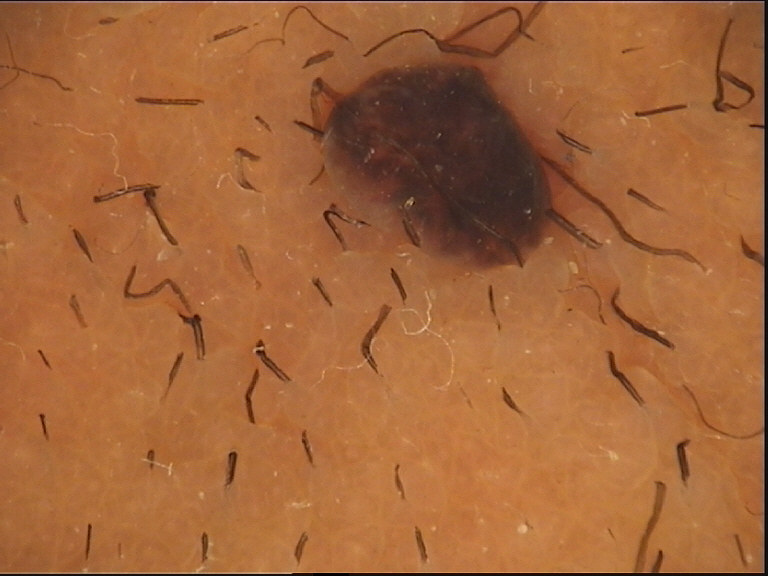A dermoscopic photograph of a skin lesion. The architecture is that of a banal lesion. Labeled as a dermal nevus.